Present for one to three months · this is a close-up image · the lesion is associated with burning, pain, darkening, bothersome appearance, enlargement and itching · located on the leg, back of the hand, head or neck, top or side of the foot and arm · the subject is a female aged 30–39 · self-categorized by the patient as a rash · the lesion is described as raised or bumpy and fluid-filled — 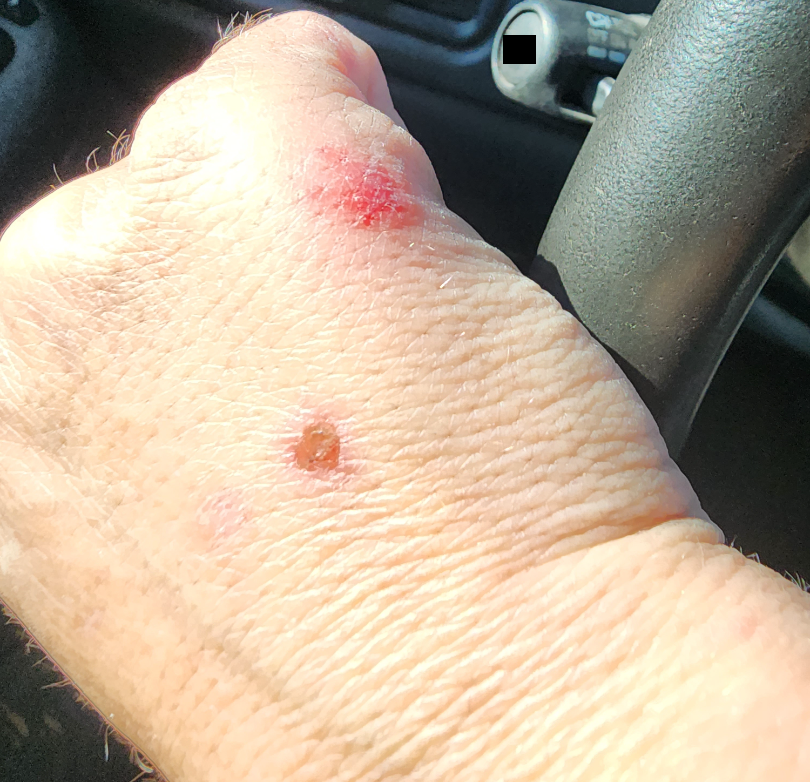assessment — not assessable.